A dermoscopic close-up of a skin lesion.
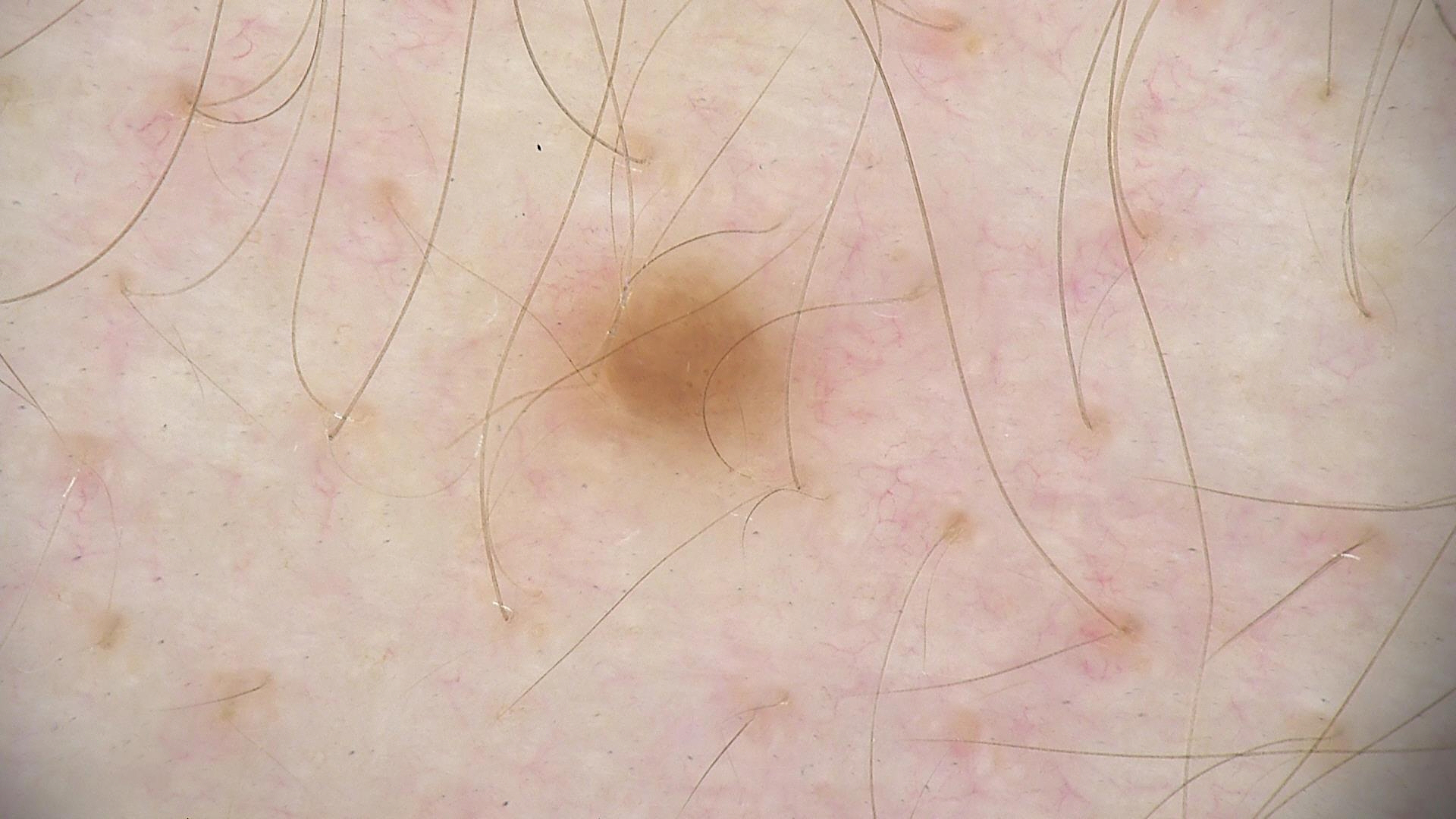category: banal
diagnosis: dermal nevus (expert consensus)